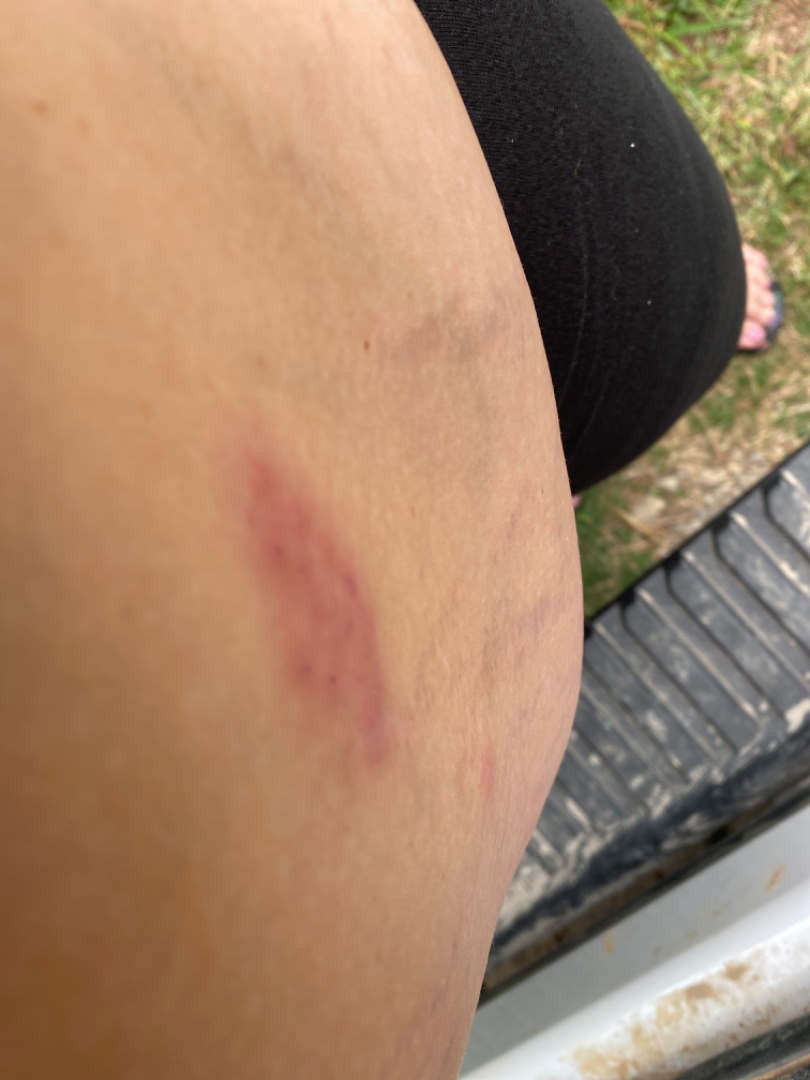The lesion is associated with burning, itching and pain. The affected area is the front of the torso. The patient reports the lesion is raised or bumpy. Self-categorized by the patient as a rash. This image was taken at an angle. The condition has been present for less than one week. On remote dermatologist review, the favored diagnosis is Herpes Zoster; also consider Herpes Simplex; less probable is Allergic Contact Dermatitis.